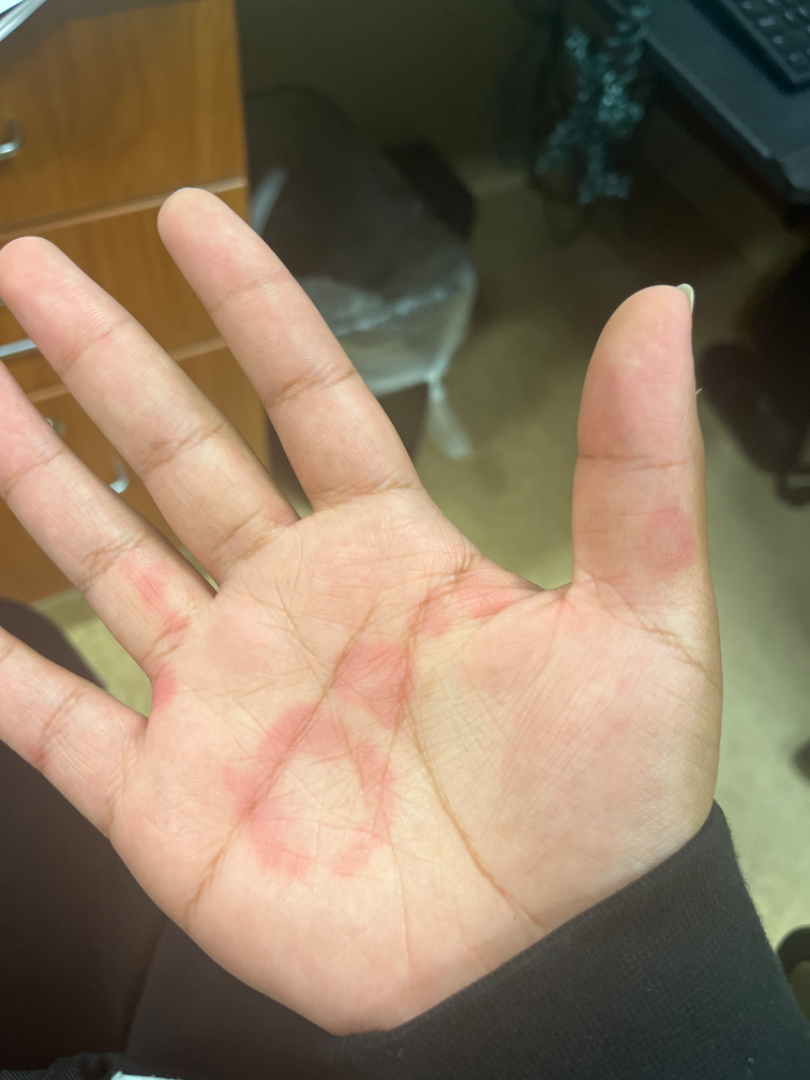The reviewing panel's impression was: most likely Urticaria; less likely is Drug Rash; lower on the differential is Erythema multiforme; less probable is Geographic tongue.